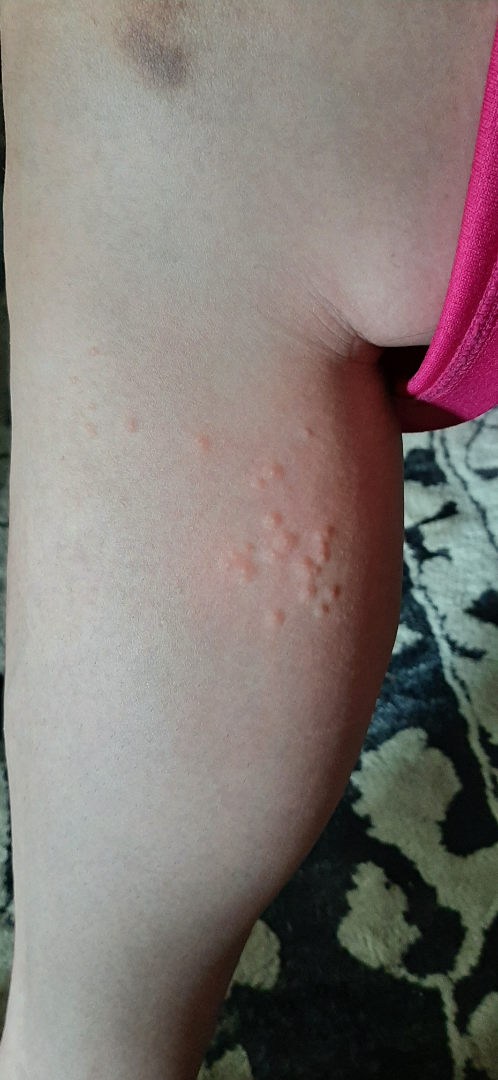<case>
  <differential>
    <leading>Insect Bite</leading>
    <considered>Allergic Contact Dermatitis</considered>
    <unlikely>Molluscum Contagiosum</unlikely>
  </differential>
</case>